An image taken at a distance, the affected area is the top or side of the foot.
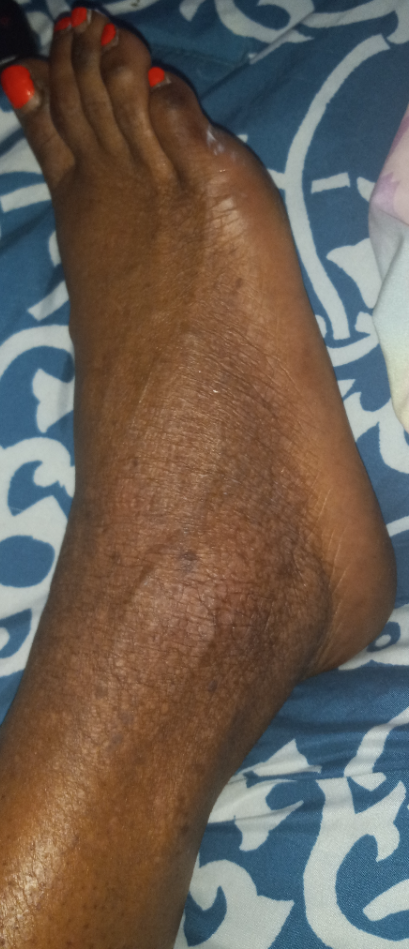assessment = ungradable on photographic review | reported symptoms = itching | duration = more than one year | patient's own categorization = a rash.